The lesion is associated with pain; no constitutional symptoms were reported; the contributor notes the lesion is raised or bumpy; the patient is a female aged 18–29; an image taken at an angle; the lesion involves the arm: 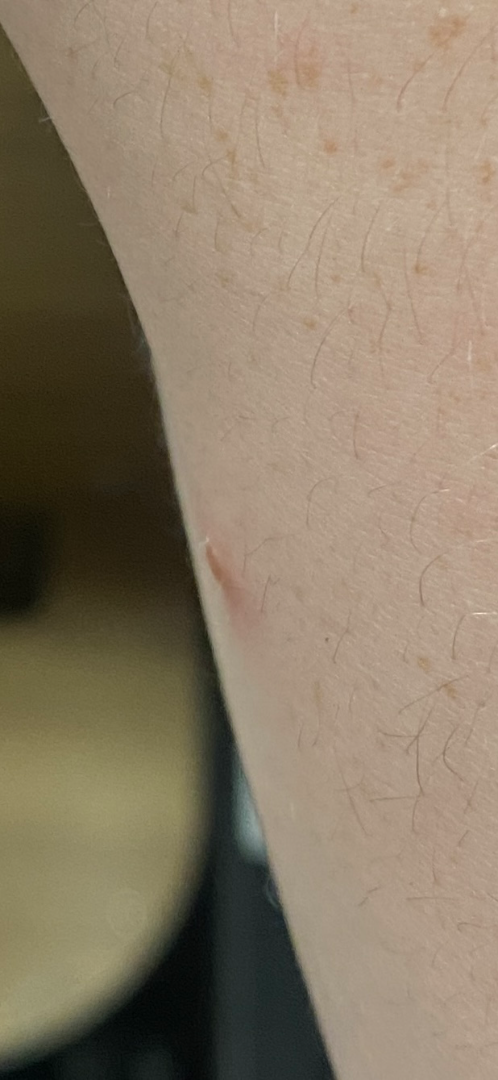differential:
  tied_lead:
    - Impetigo
    - Insect Bite